The photograph is a close-up of the affected area.
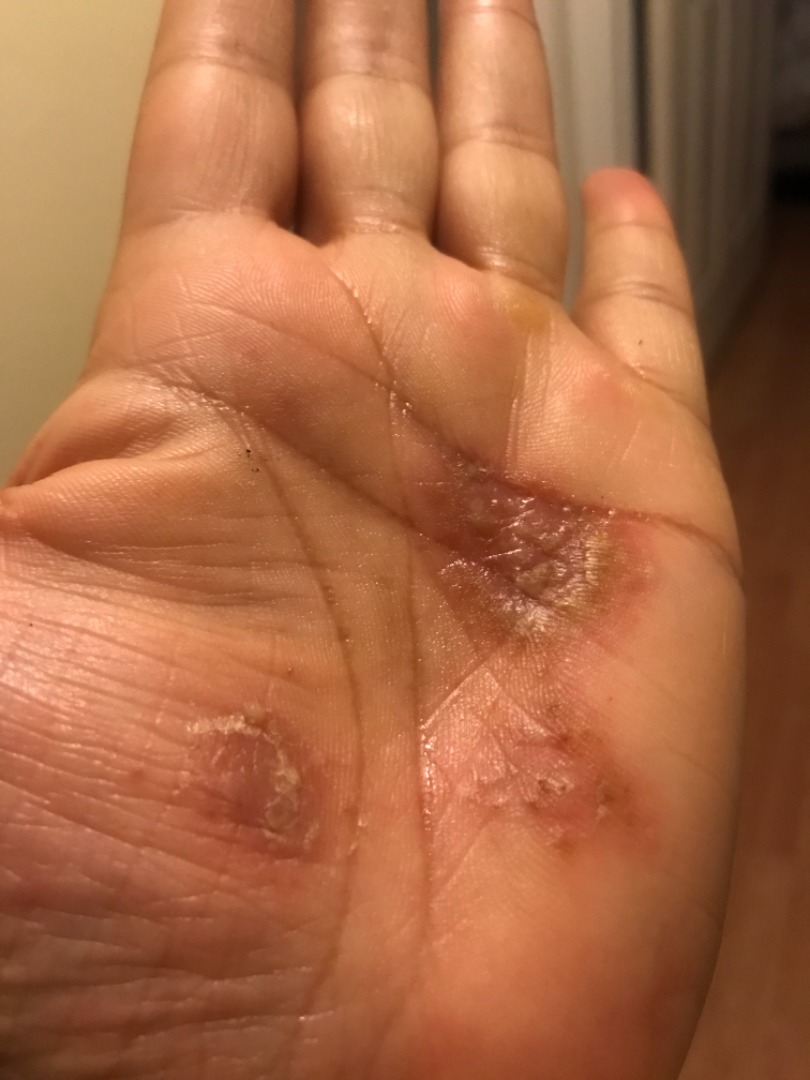On photographic review, most consistent with Eczema; also consider Psoriasis; an alternative is Allergic Contact Dermatitis.